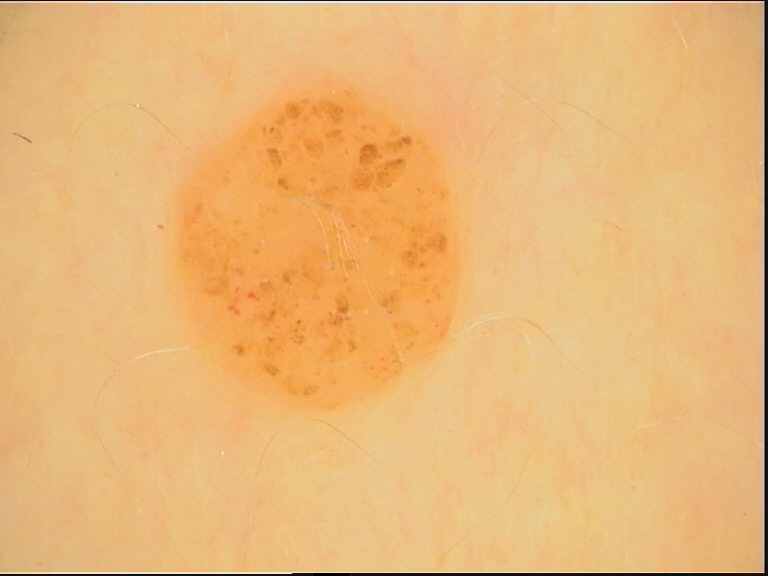diagnosis = compound nevus (expert consensus).